The patient is male. Close-up view. The affected area is the head or neck: 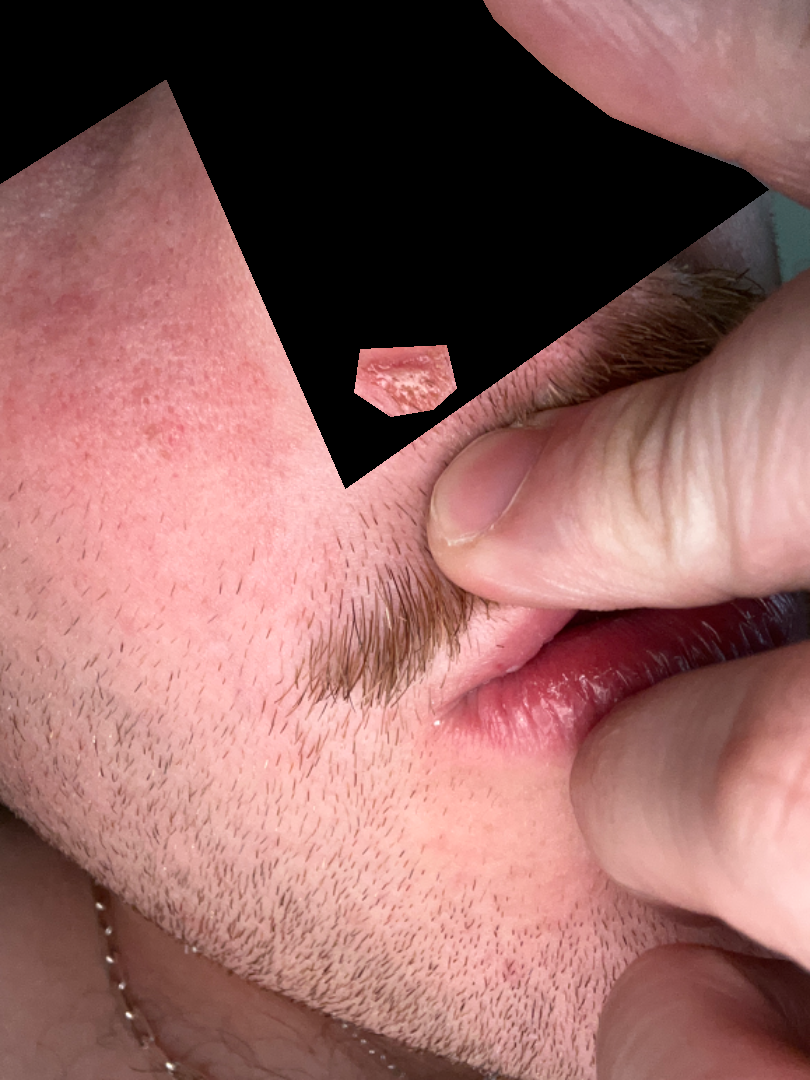Q: What was the assessment?
A: indeterminate
Q: What is the patient's skin tone?
A: Fitzpatrick skin type II
Q: What symptoms does the patient report?
A: none reported
Q: When did this start?
A: about one day
Q: Constitutional symptoms?
A: none reported
Q: Texture?
A: rough or flaky
Q: Patient's own categorization?
A: acne